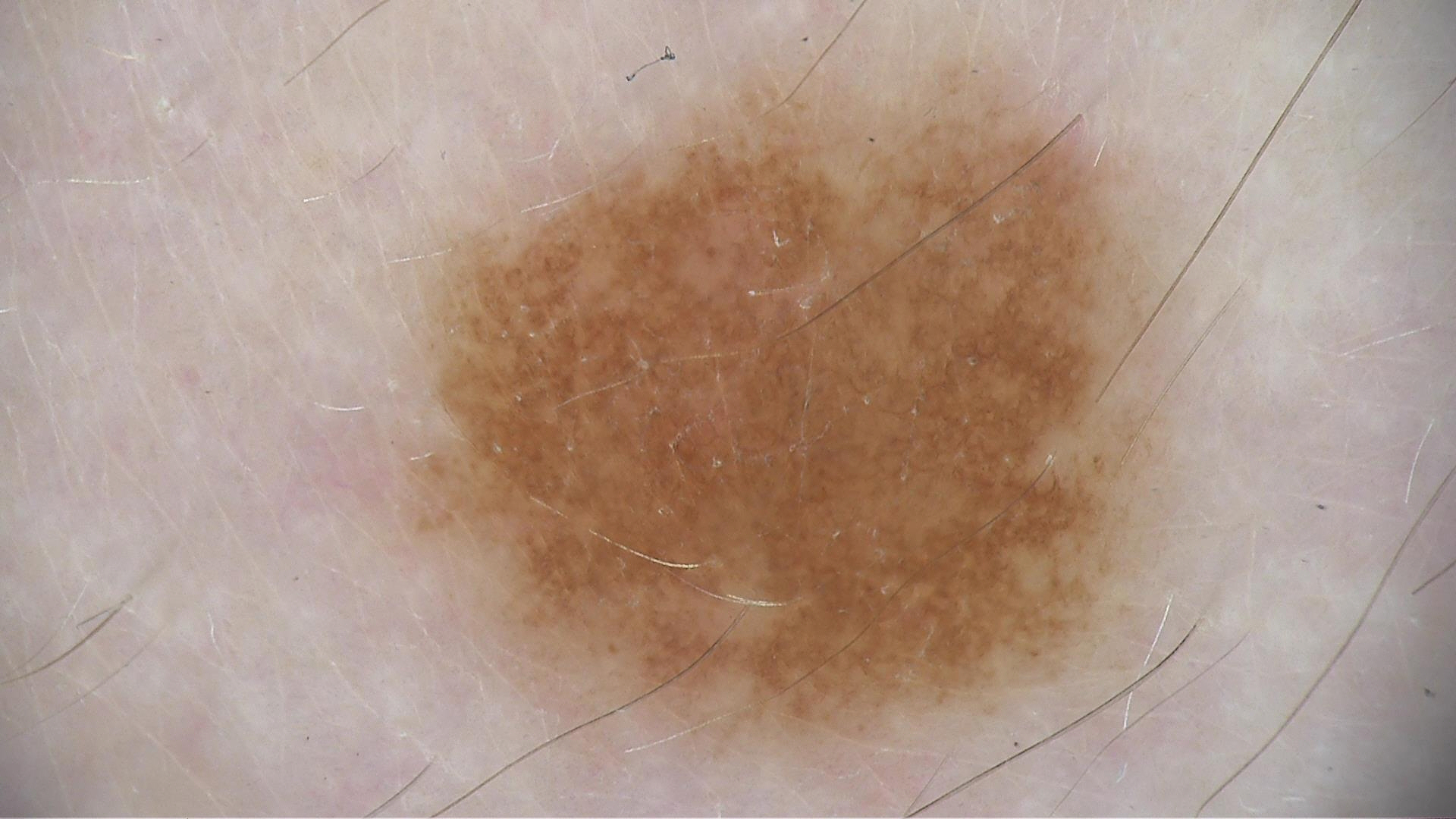Case:
* image type: dermatoscopy
* label: compound nevus (expert consensus)